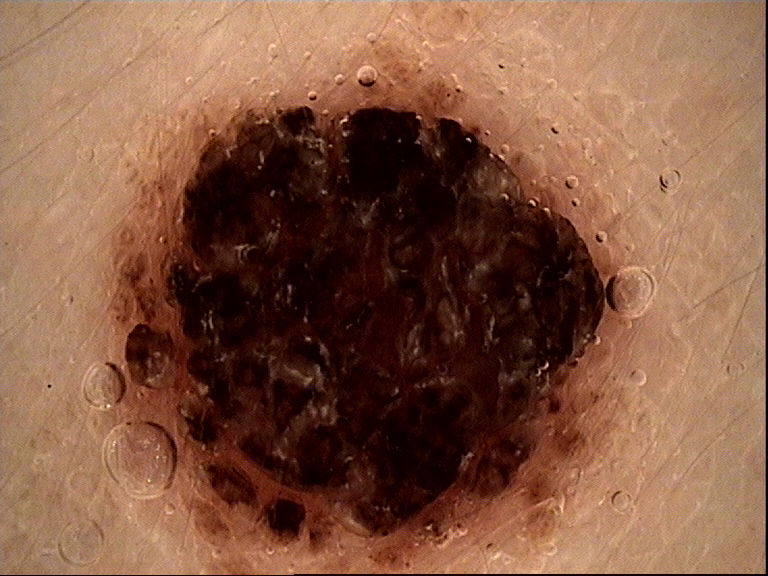A dermoscopic image of a skin lesion. Consistent with a banal lesion — a compound nevus.